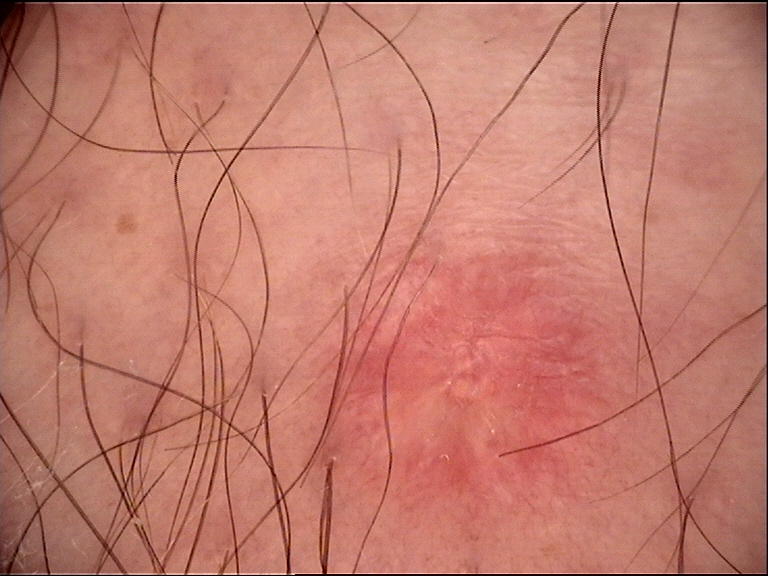diagnostic label — dermatofibroma (expert consensus).